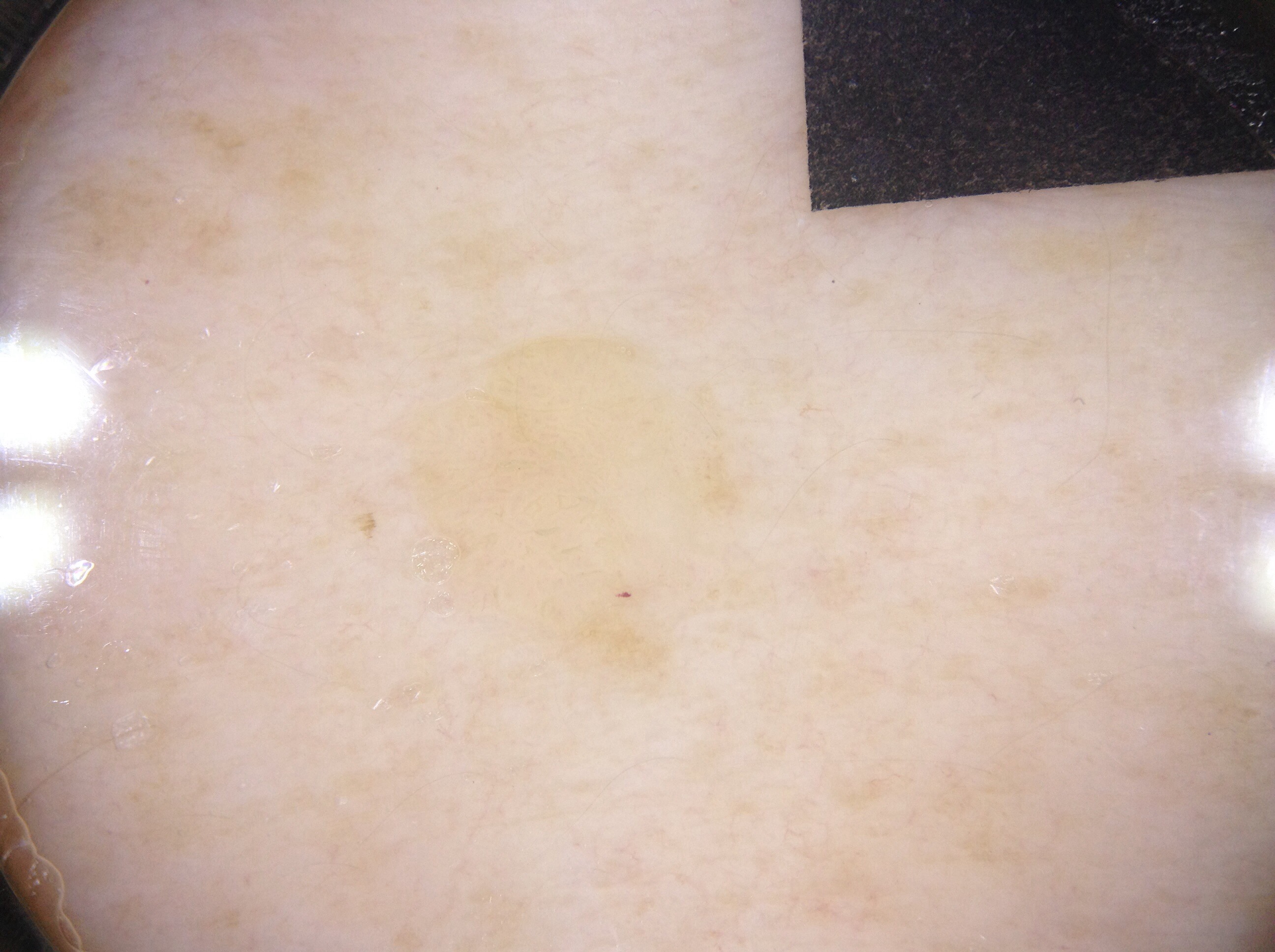Q: What is the imaging modality?
A: dermoscopy
Q: Who is the patient?
A: female, in their 60s
Q: Lesion extent?
A: ~6% of the field
Q: What dermoscopic features are present?
A: pigment network; absent: streaks, negative network, and milia-like cysts
Q: Where is the lesion in the image?
A: [418,335,737,677]
Q: What is this lesion?
A: a seborrheic keratosis